A dermoscopy image of a single skin lesion · the subject is a female aged 18 to 22.
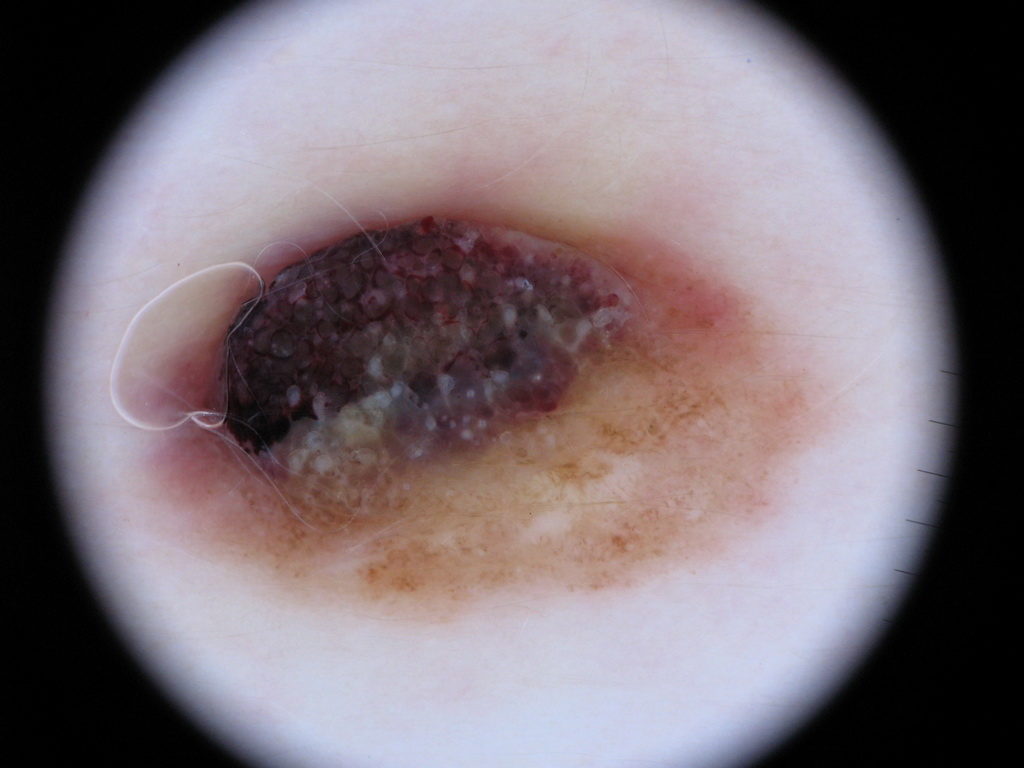lesion location: 130/170/862/633 | dermoscopic features: pigment network | size: large | impression: a melanocytic nevus, a benign skin lesion.